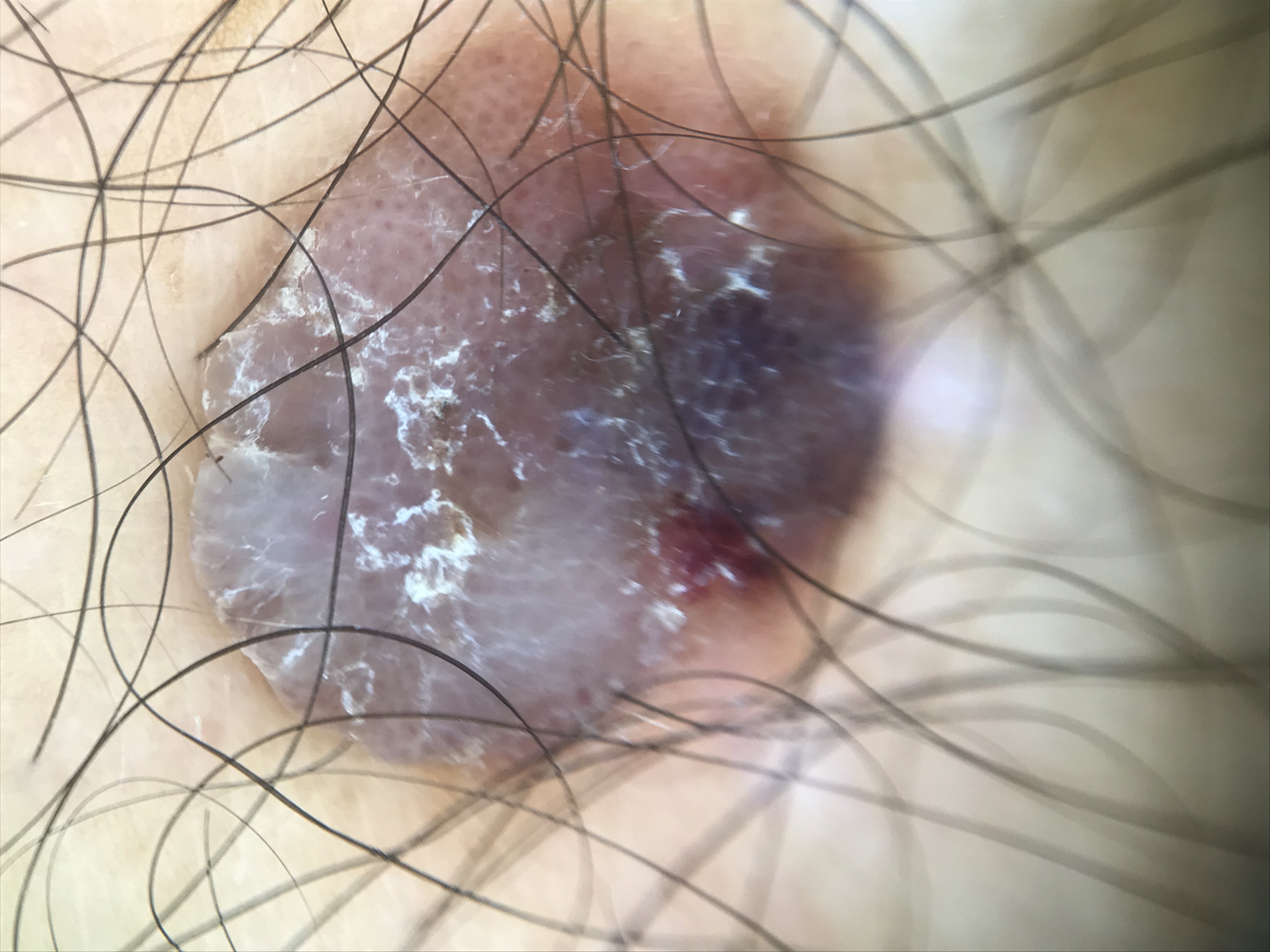A skin lesion imaged with a dermatoscope. Classified as a keratinocytic lesion — a seborrheic keratosis.